A male subject, in their 70s; a dermoscopic close-up of a skin lesion: 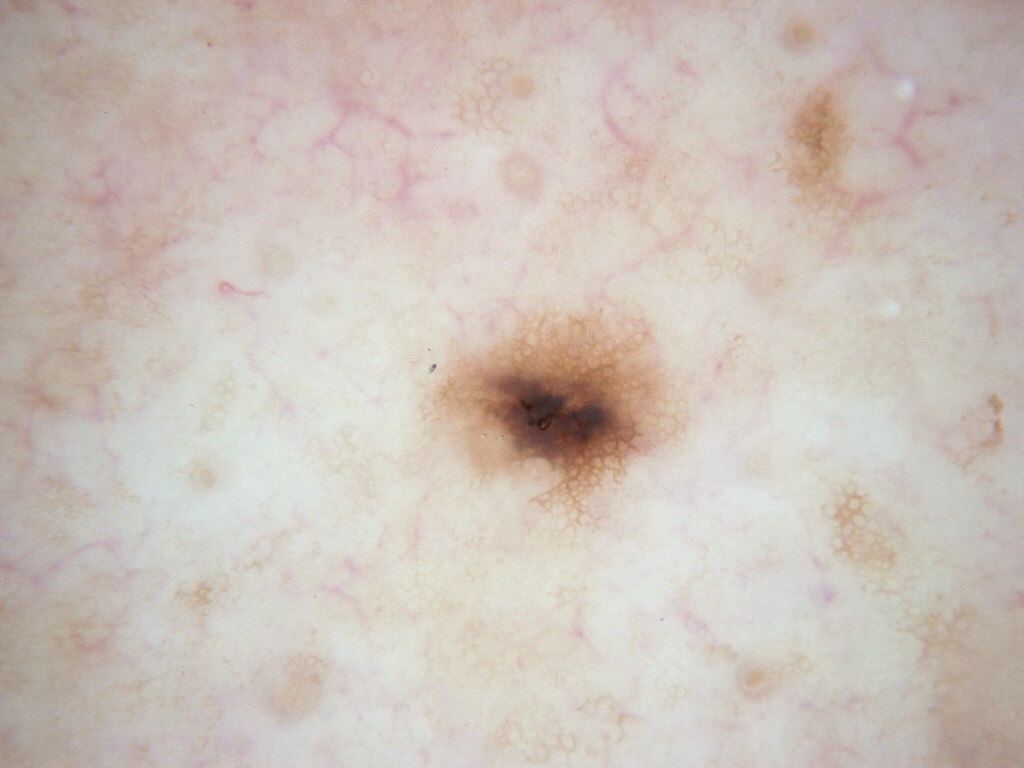dermoscopic findings = pigment network; absent: globules, streaks, milia-like cysts, and negative network | location = (403, 276, 701, 564) | diagnosis = a melanocytic nevus, a benign lesion.